A dermoscopic view of a skin lesion · the patient is female:
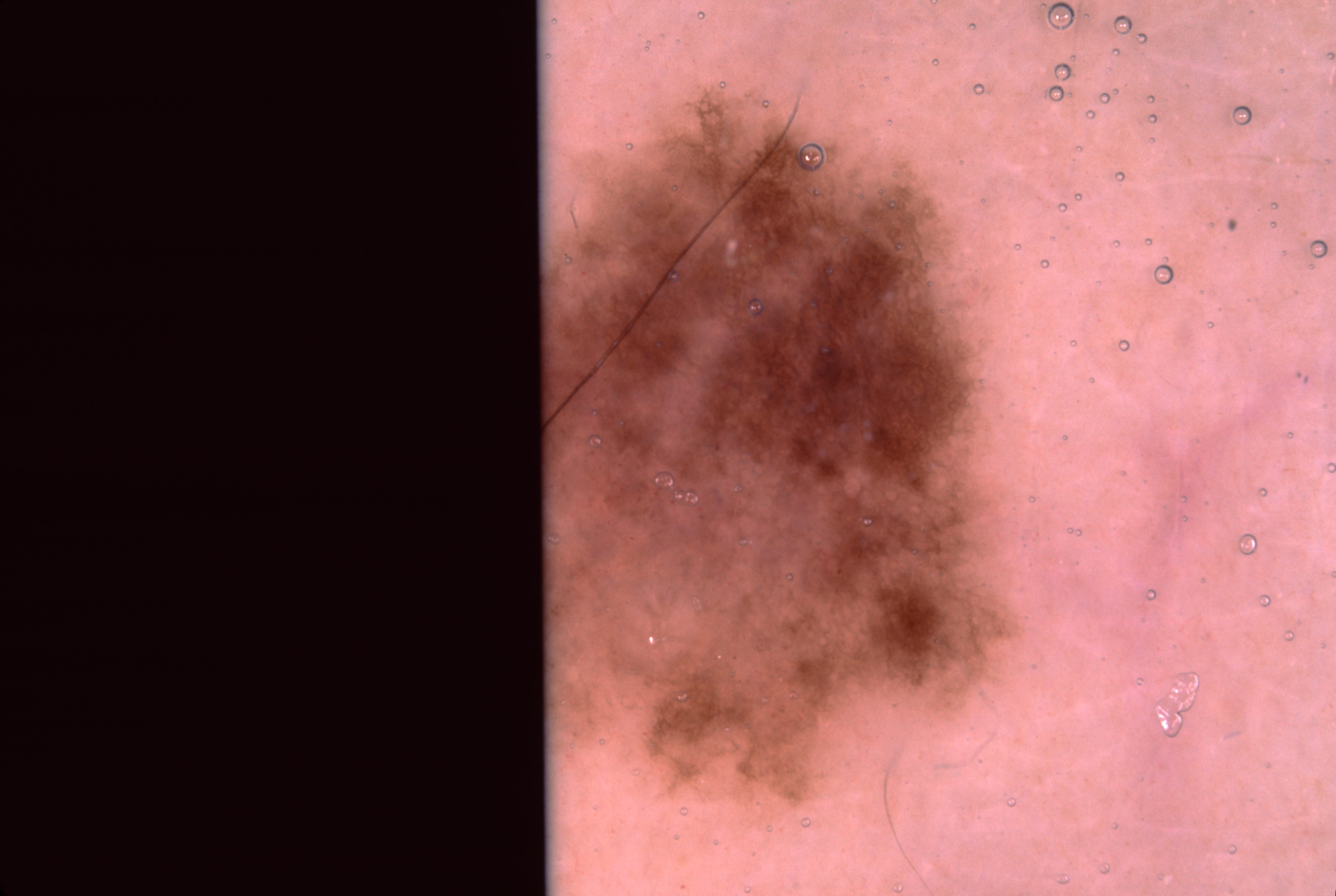Q: How does the lesion relate to the field edge?
A: reaches the image border
Q: How much of the field does the lesion occupy?
A: ~22% of the field
Q: Where is the lesion in the image?
A: [533, 0, 1019, 895]
Q: What does dermoscopy show?
A: pigment network; absent: streaks, negative network, and milia-like cysts
Q: What is the diagnosis?
A: a melanocytic nevus